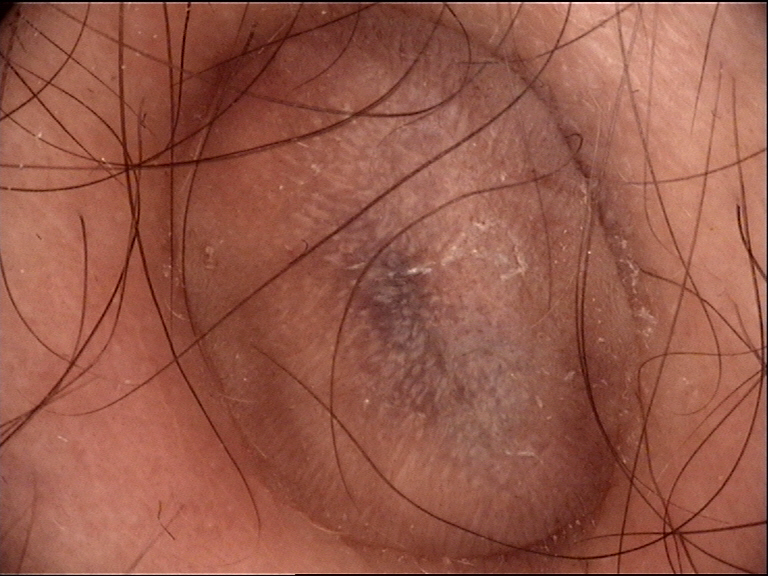imaging — dermatoscopy | label — dermatofibroma (expert consensus).